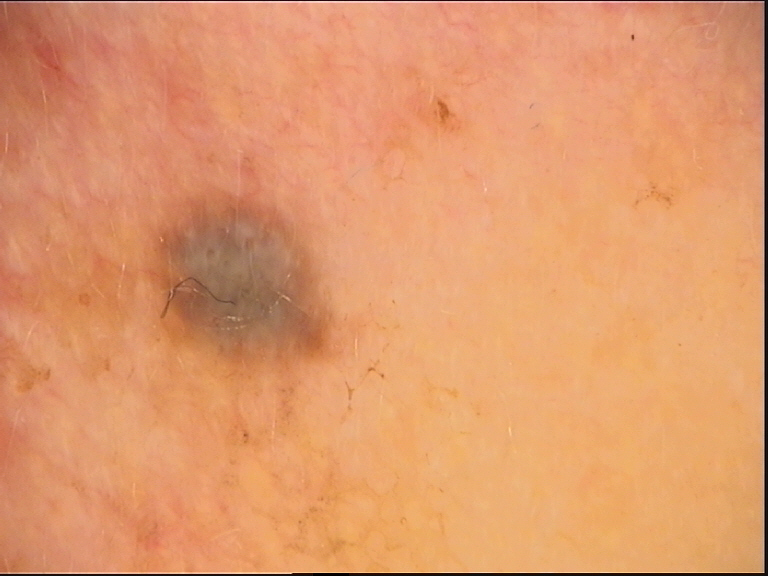image: dermatoscopy | classification: dermal, banal | diagnostic label: blue nevus (expert consensus).